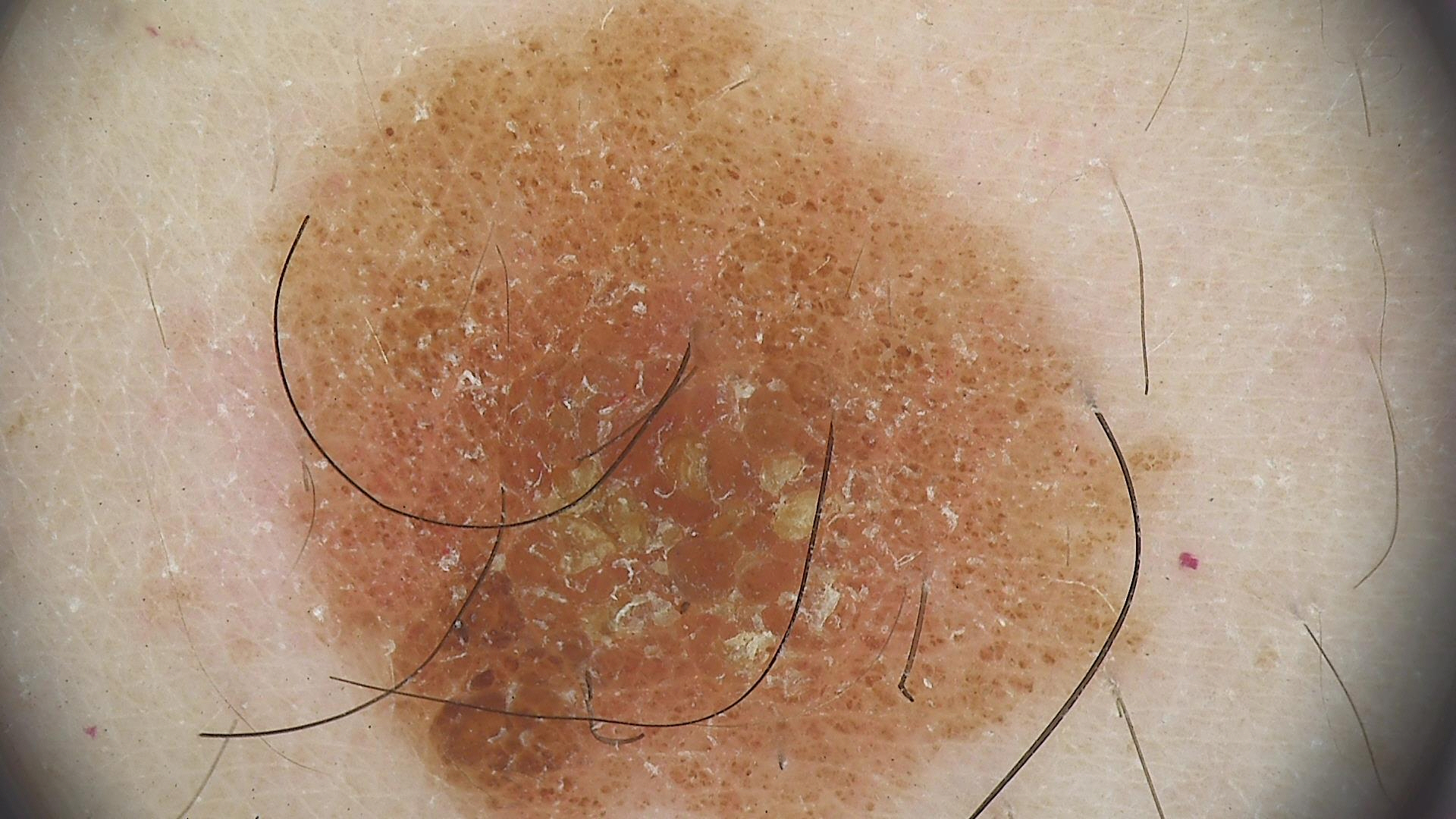A dermoscopic image of a skin lesion.
The morphology is that of a banal lesion.
Diagnosed as a compound nevus.